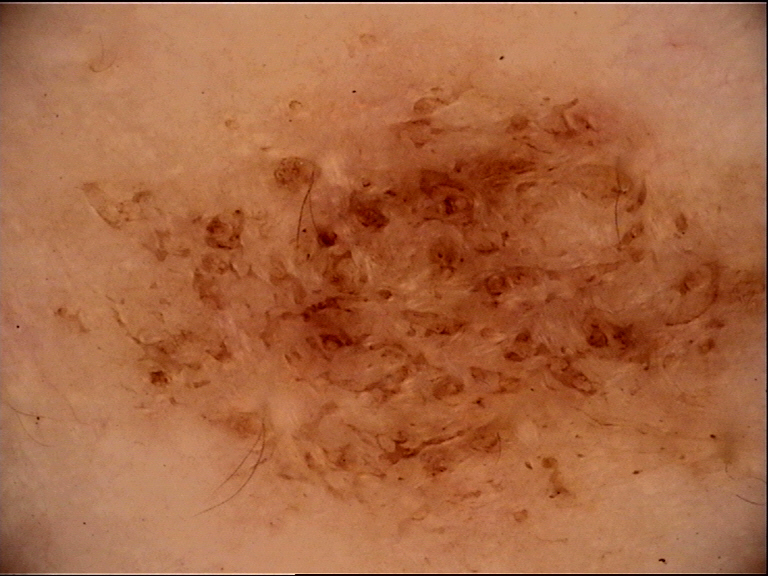Case:
* class — dysplastic compound nevus (expert consensus)